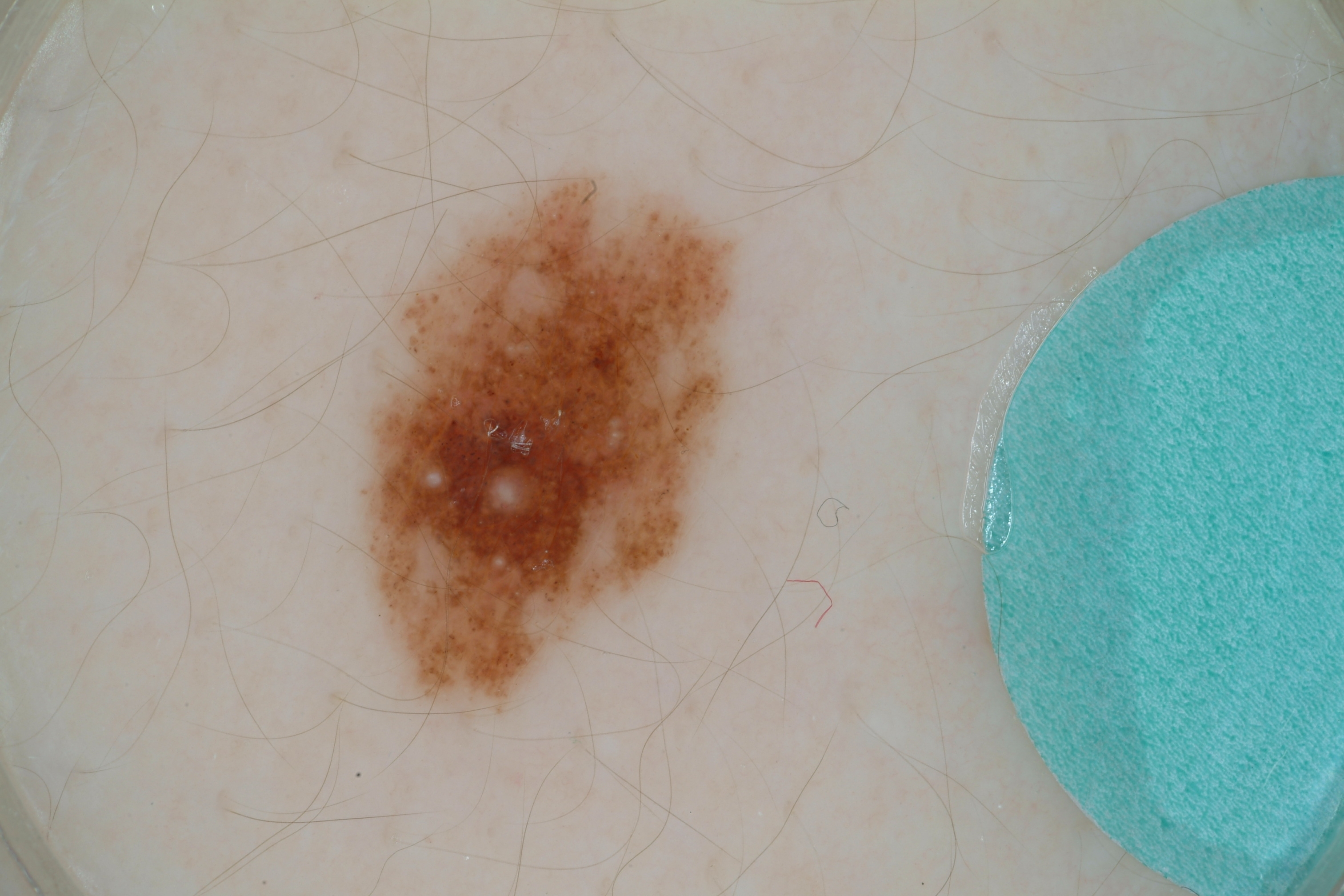image type — dermatoscopic image of a skin lesion | patient — male, aged 13-17 | location — x1=357, y1=165, x2=745, y2=719 | features — milia-like cysts, globules, and pigment network; absent: streaks and negative network | extent — moderate | assessment — a melanocytic nevus.